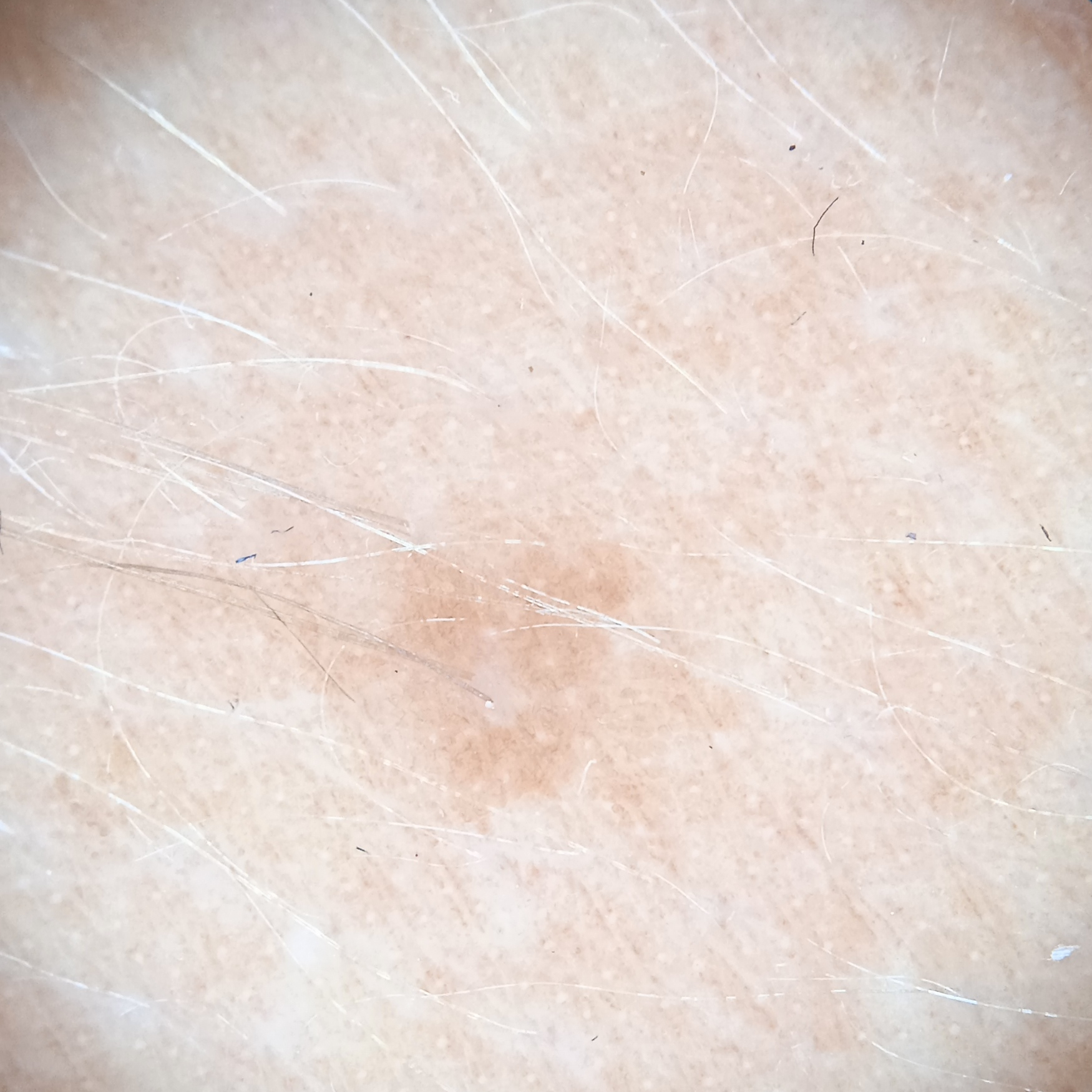The reviewing dermatologists could not reach a confident diagnosis. Case summary: The patient says their skin tans without first burning. A female patient 47 years of age. A moderate number of moles by the patient's own estimate. Acquired for a research image collection, with no referral diagnosis. The patient reports a history of sunbed use. The lesion is located on the back.